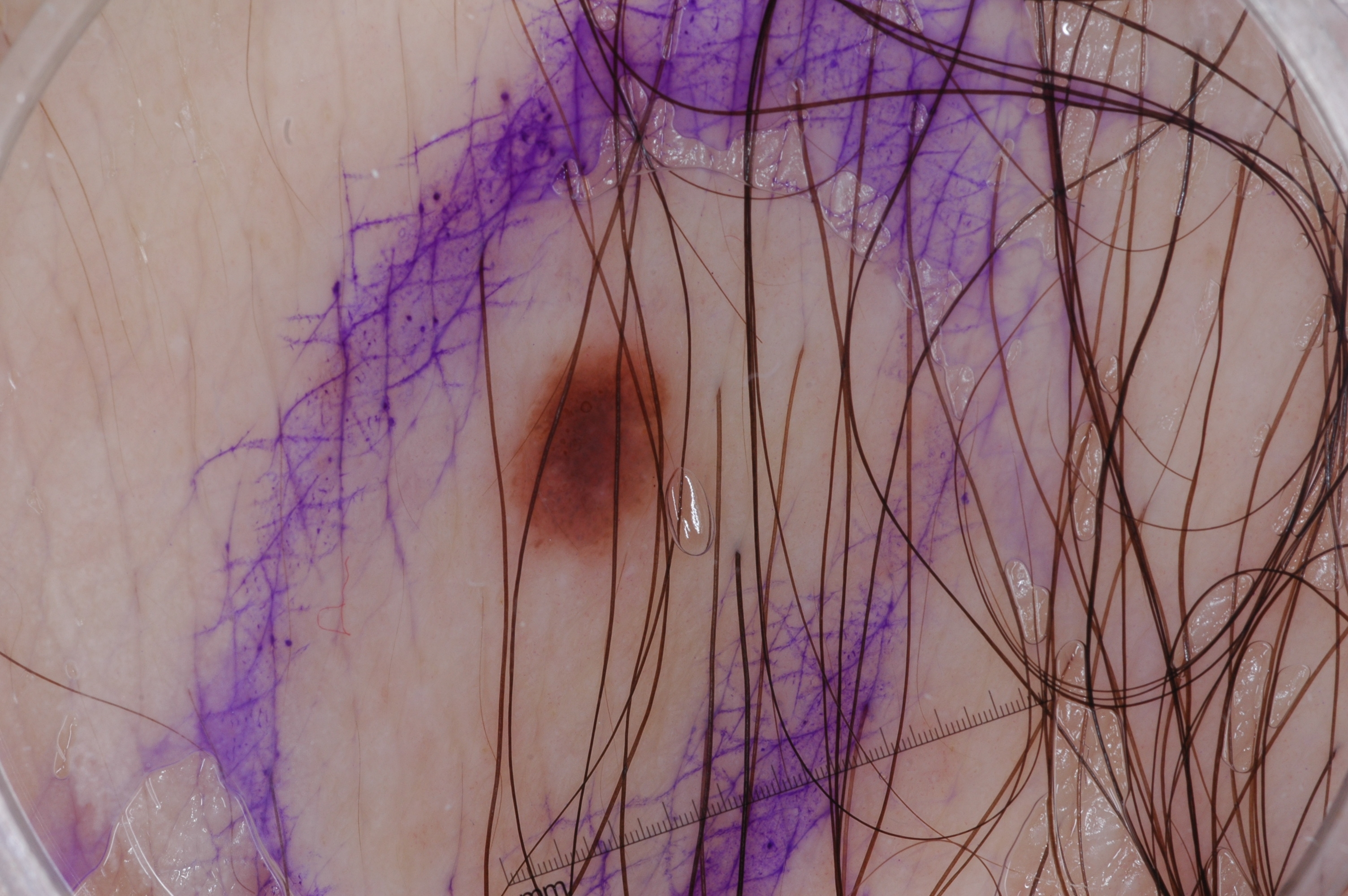A male subject, roughly 55 years of age.
A dermatoscopic image of a skin lesion.
On dermoscopy, the lesion shows no milia-like cysts, streaks, negative network, or pigment network.
The lesion covers approximately 2% of the dermoscopic field.
The lesion is bounded by 505, 343, 674, 561.
Clinically diagnosed as a melanocytic nevus, a benign skin lesion.